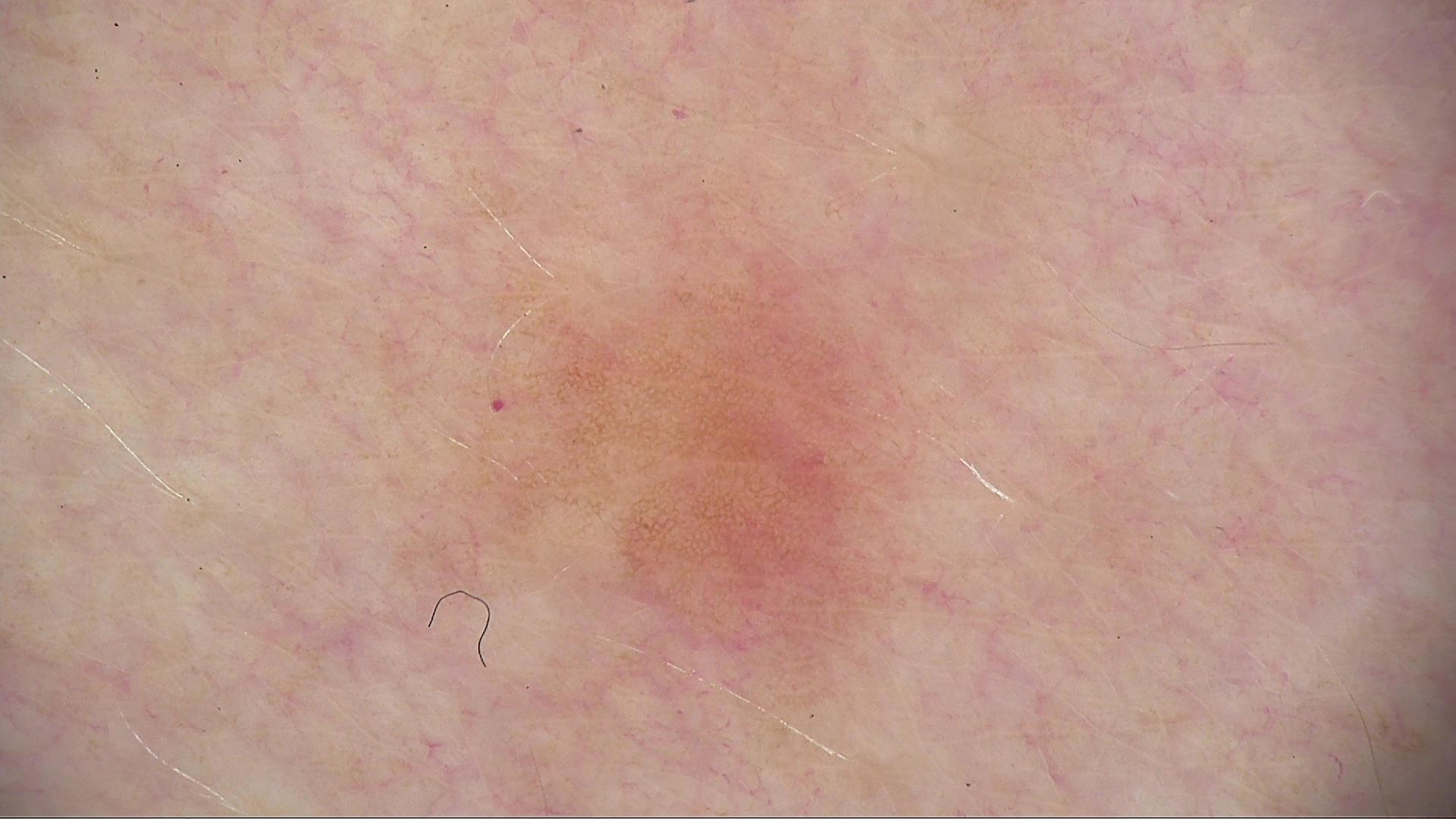Labeled as a lentigo simplex.